The back of the hand is involved; no associated systemic symptoms reported; self-categorized by the patient as a rash; close-up view; present for less than one week: 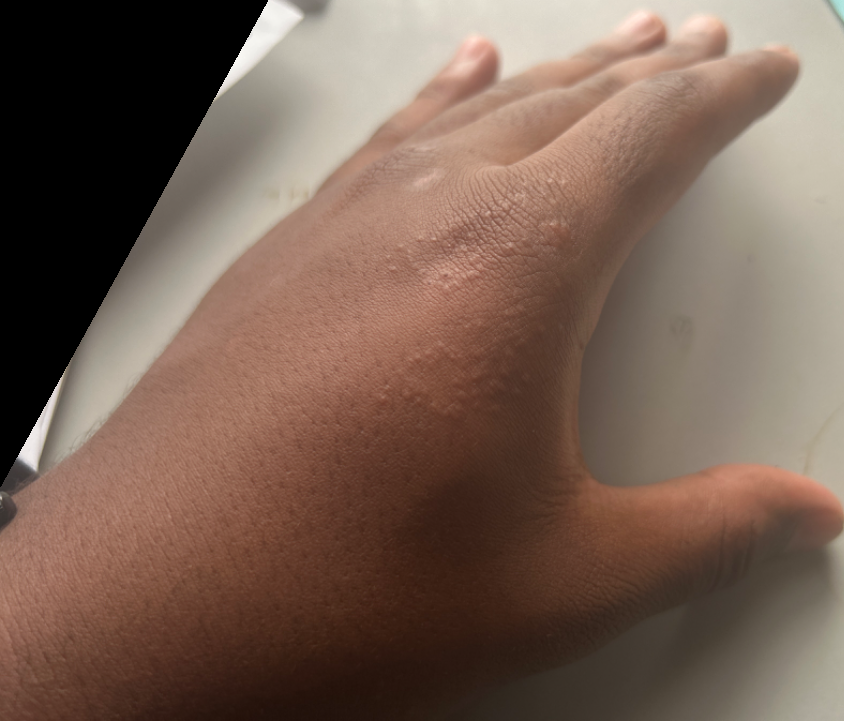The condition could not be reliably identified from the image.